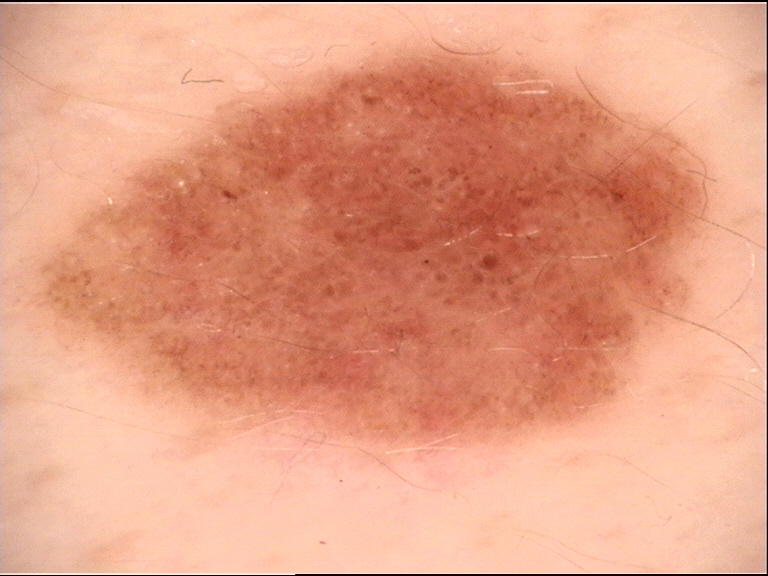The diagnostic label was a dysplastic compound nevus.